The photo was captured at an angle:
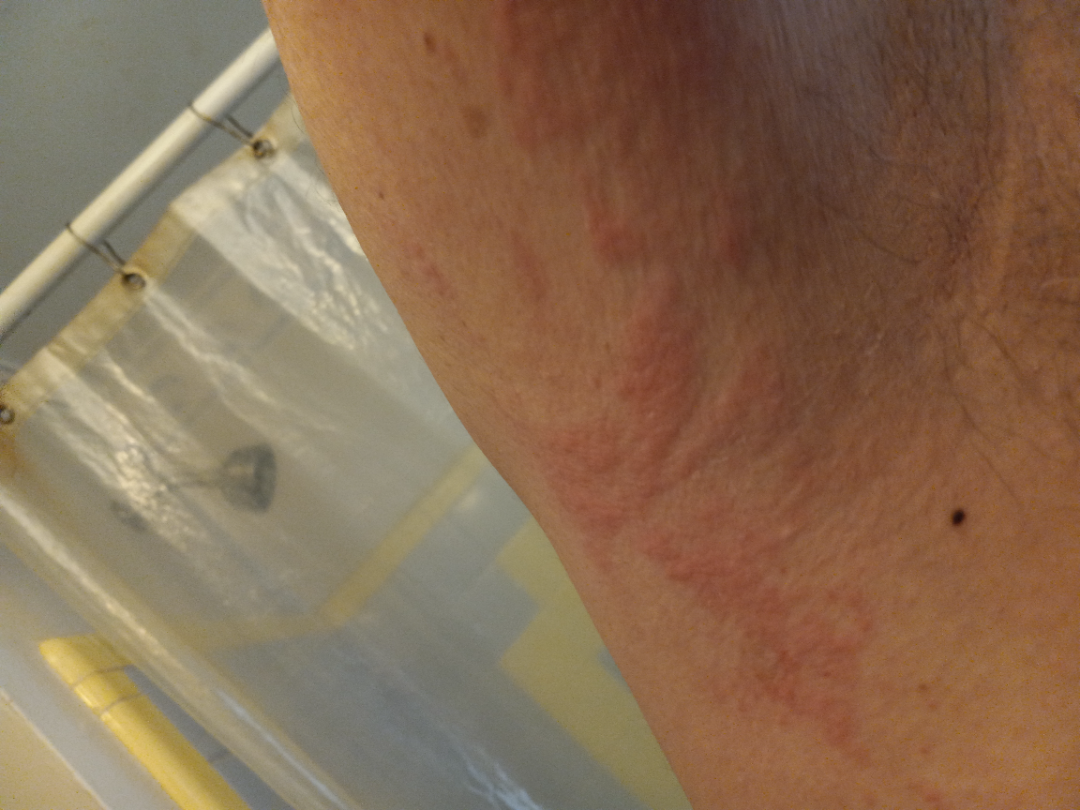Reviewed remotely by one dermatologist: the reviewer's impression was Urticaria.